Dermoscopy of a skin lesion:
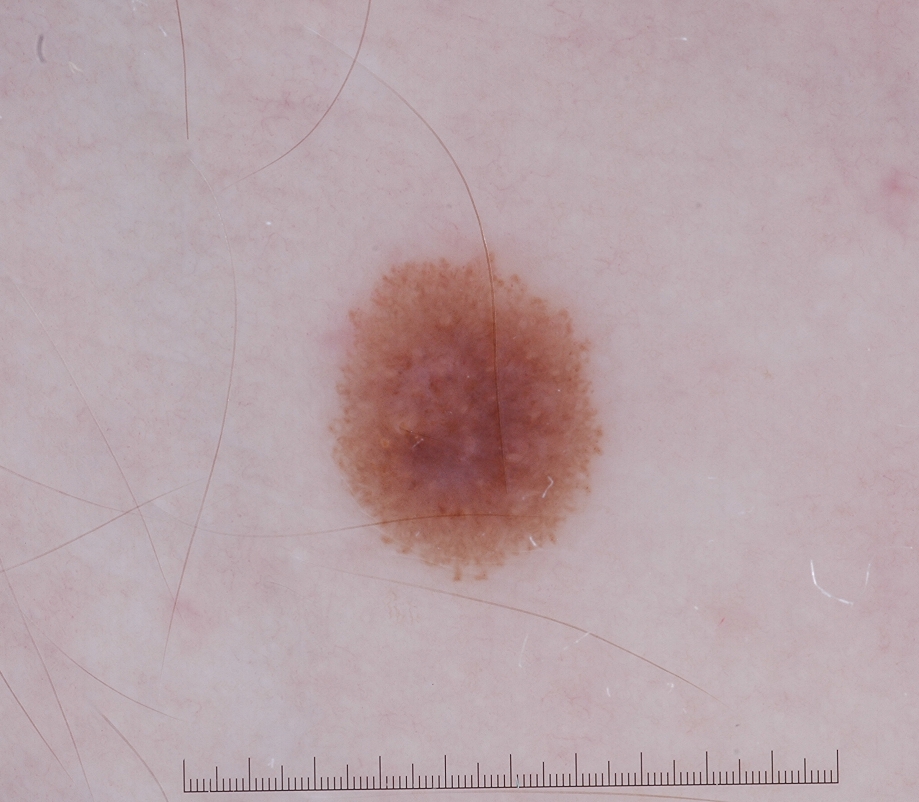Findings:
The lesion occupies roughly 10% of the field. Dermoscopic review identifies globules. With coordinates (x1, y1, x2, y2), the lesion is located at [322, 248, 608, 586].
Impression:
The lesion was assessed as a melanocytic nevus, a benign skin lesion.